A dermoscopic image of a skin lesion.
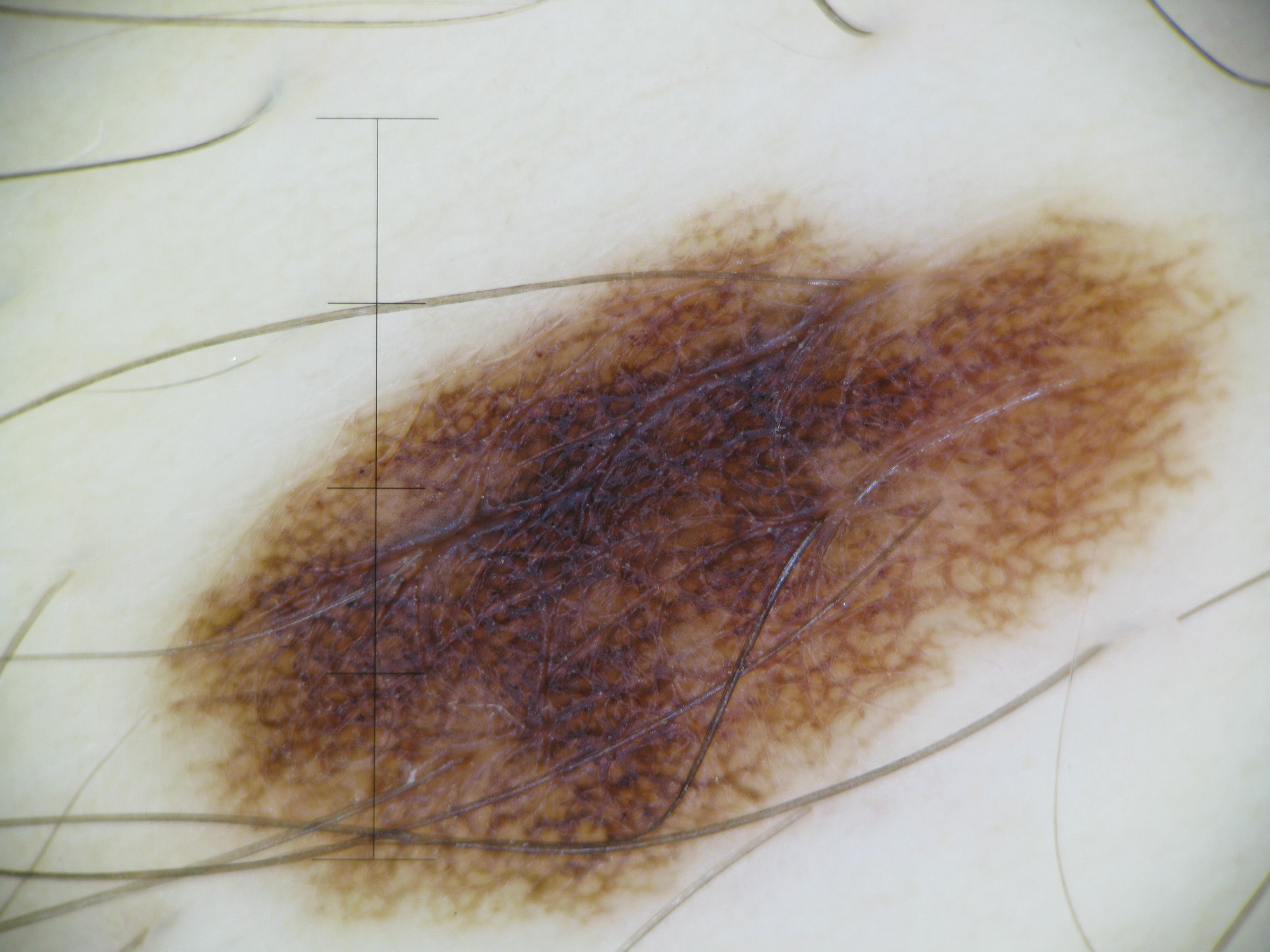class: dysplastic junctional nevus (expert consensus).